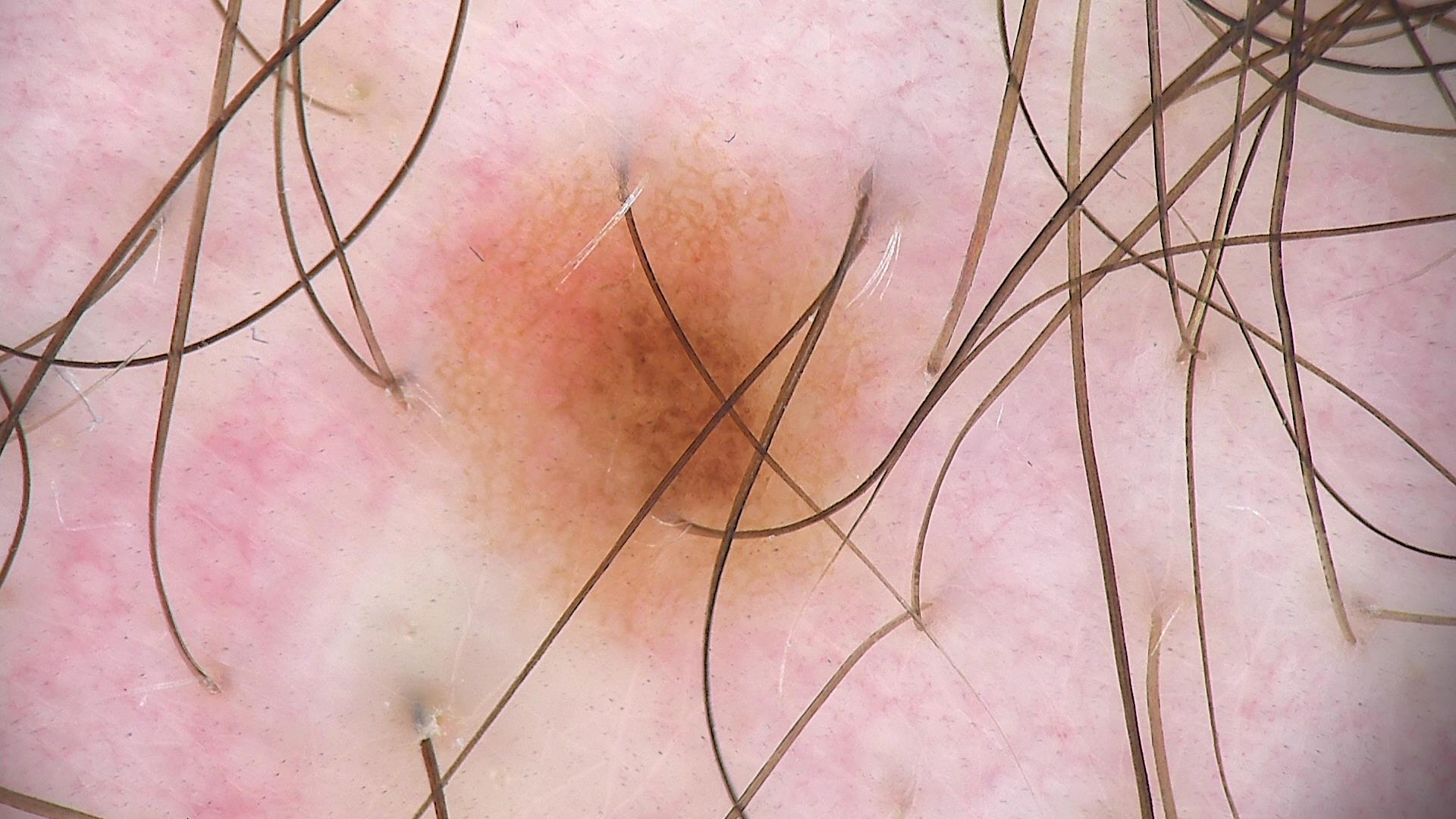Classified as a compound nevus.